A dermoscopic close-up of a skin lesion.
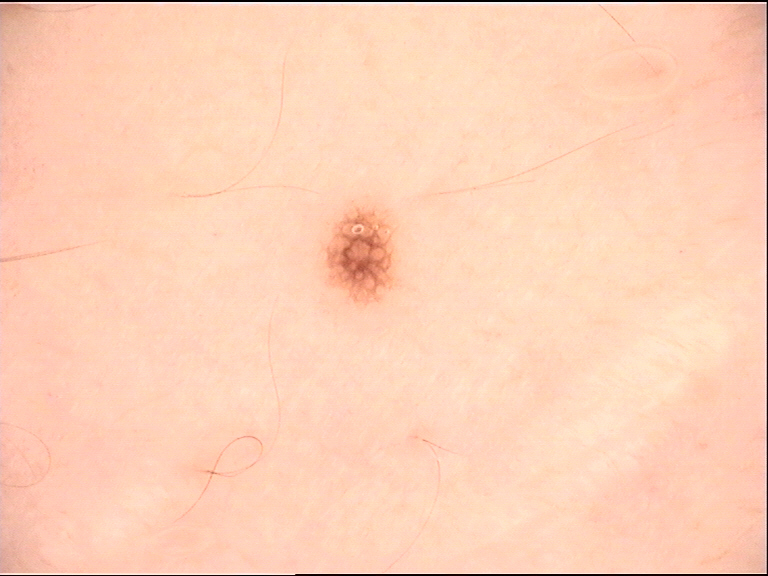{
  "diagnosis": {
    "name": "dysplastic junctional nevus",
    "code": "jd",
    "malignancy": "benign",
    "super_class": "melanocytic",
    "confirmation": "expert consensus"
  }
}